A dermatoscopic image of a skin lesion.
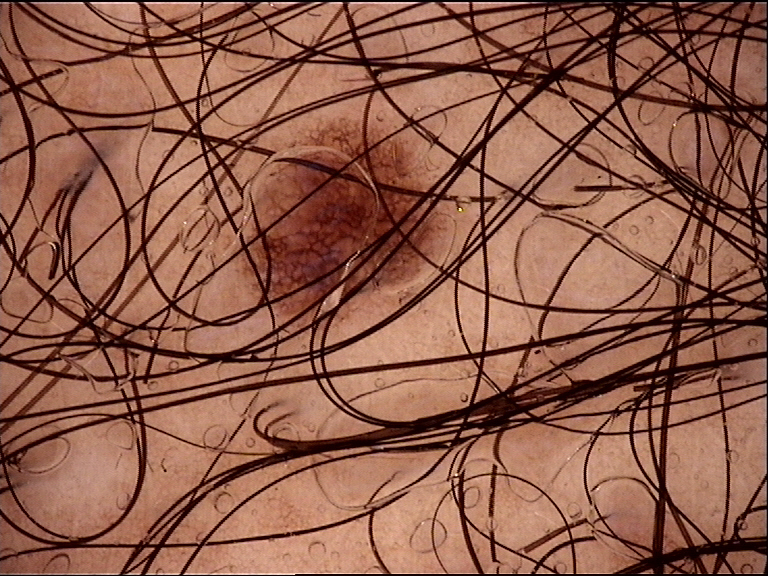assessment: junctional nevus (expert consensus).